A dermatoscopic image of a skin lesion: 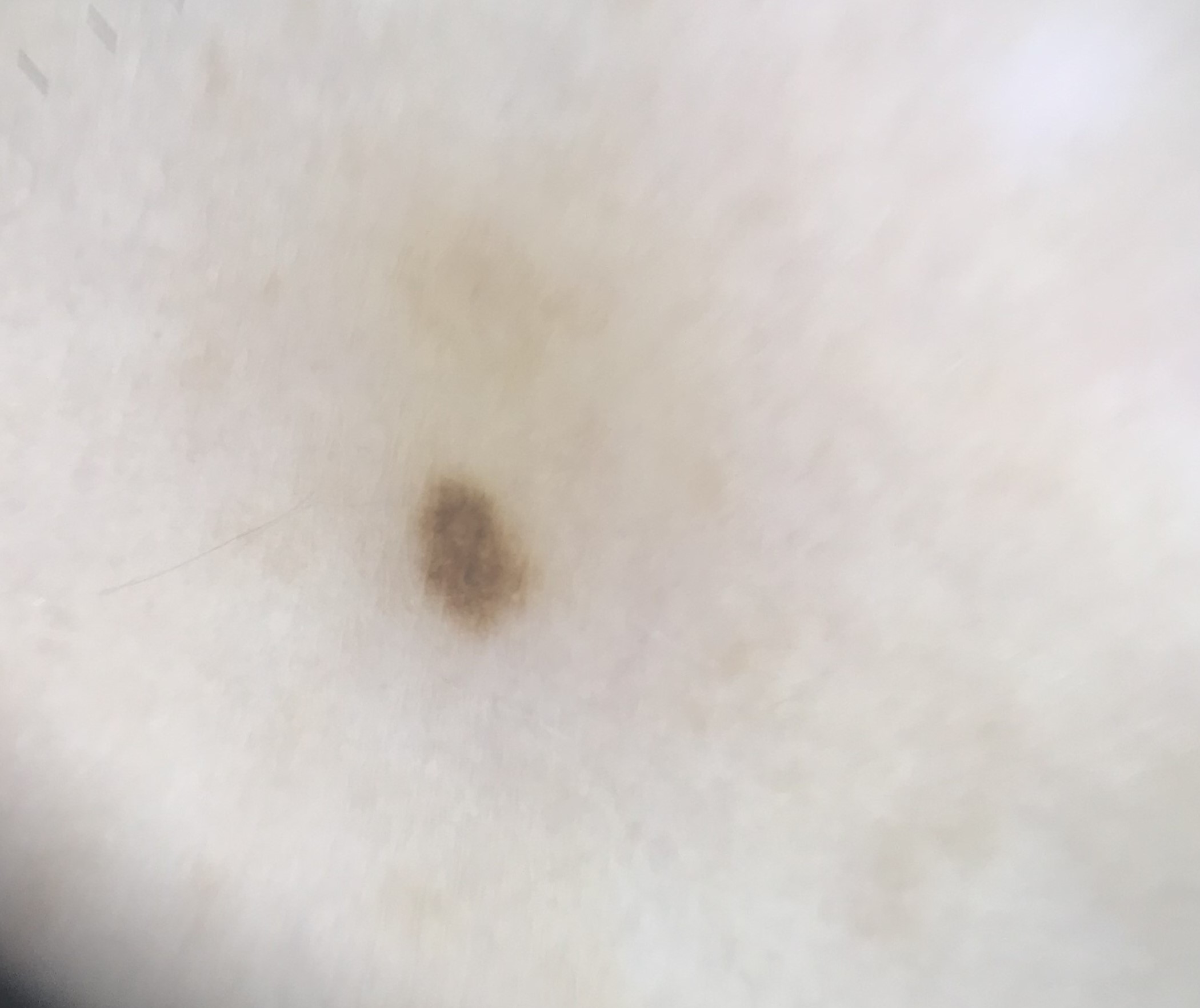Diagnosed as an acral dysplastic junctional nevus.